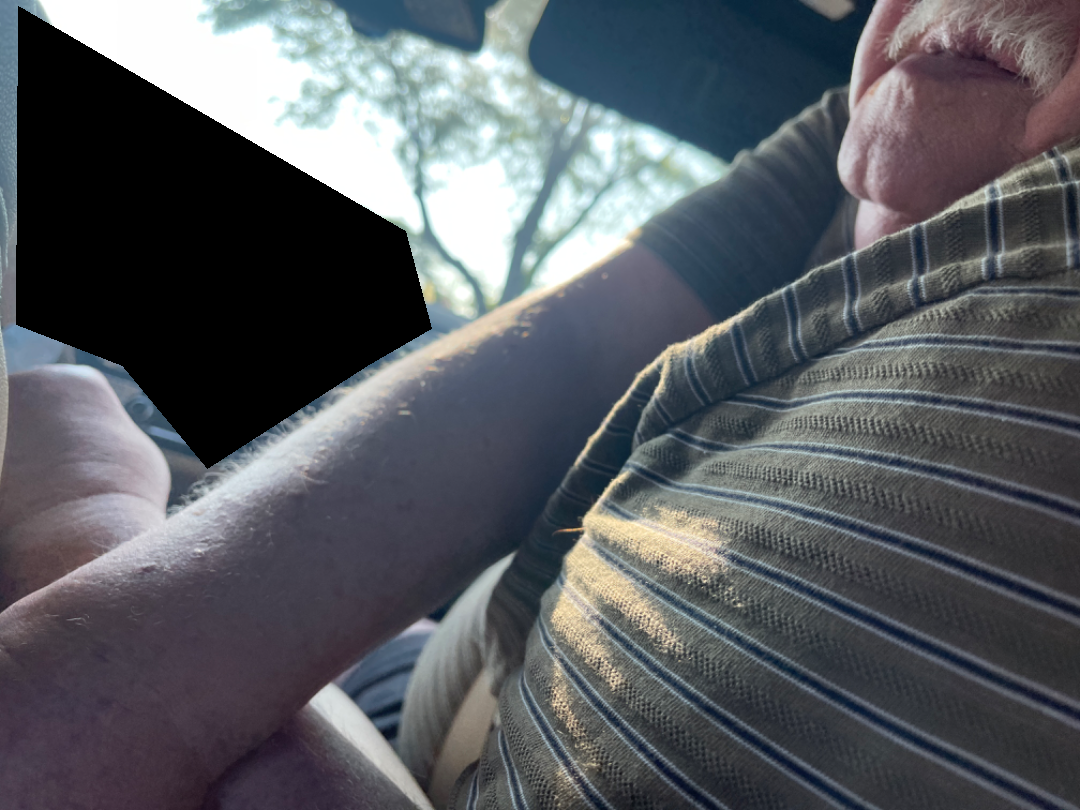Impression: The reviewing dermatologists' impression was: Drug Rash, Psoriasis and Eczema were considered with similar weight.